The photograph was taken at an angle, the leg and arm are involved, self-categorized by the patient as a rash: 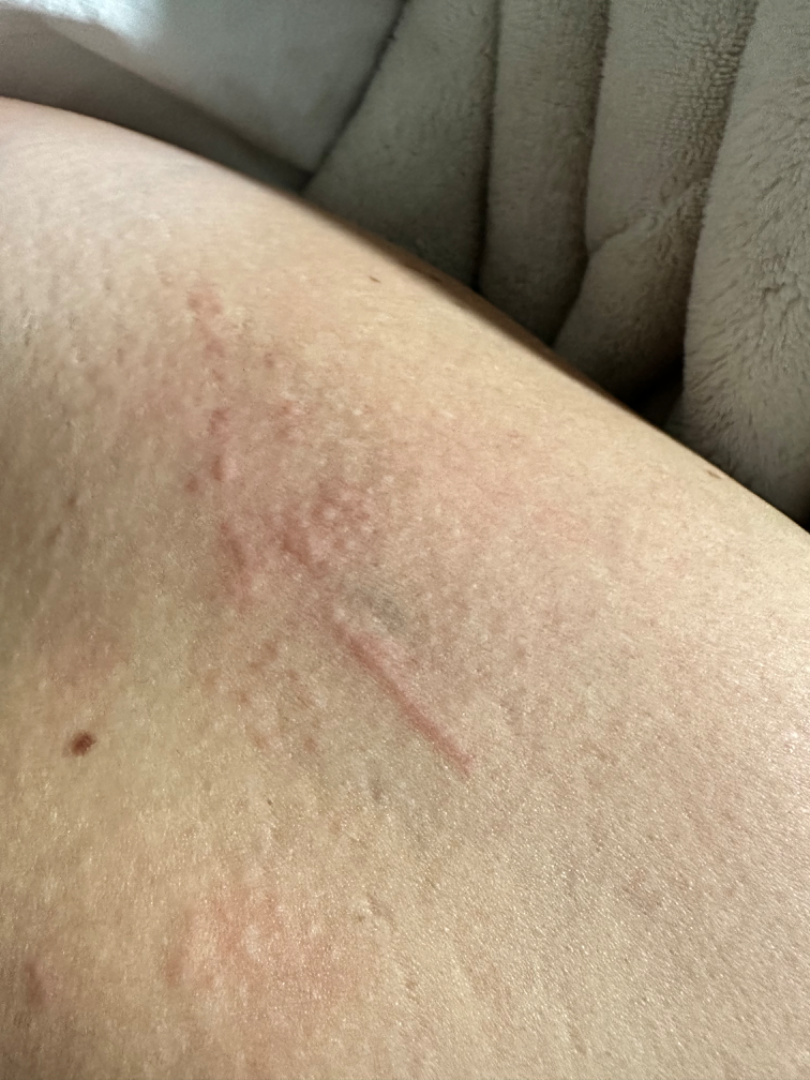The dermatologist could not determine a likely condition from the photograph alone.